The photograph was taken at an angle · the subject is a male aged 18–29 · the front of the torso, back of the torso and arm are involved — 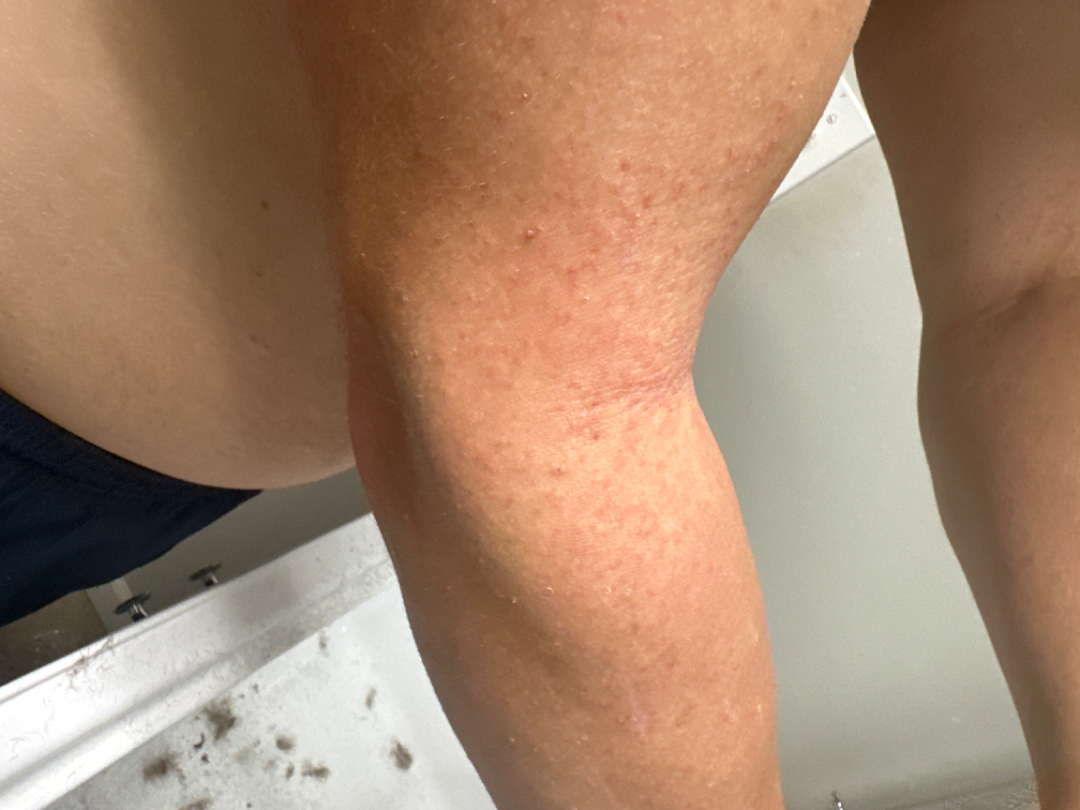| field | value |
|---|---|
| lesion symptoms | pain, itching and bothersome appearance |
| symptom duration | about one day |
| patient describes the issue as | a rash |
| surface texture | flat and rough or flaky |
| clinical impression | Eczema, Hypersensitivity and Allergic Contact Dermatitis were considered with similar weight |